The chart notes alcohol use, tobacco use, pesticide exposure, prior malignancy (patient or family), and no prior skin cancer (patient or family); a clinical close-up photograph of a skin lesion; the patient was assessed as Fitzpatrick II — 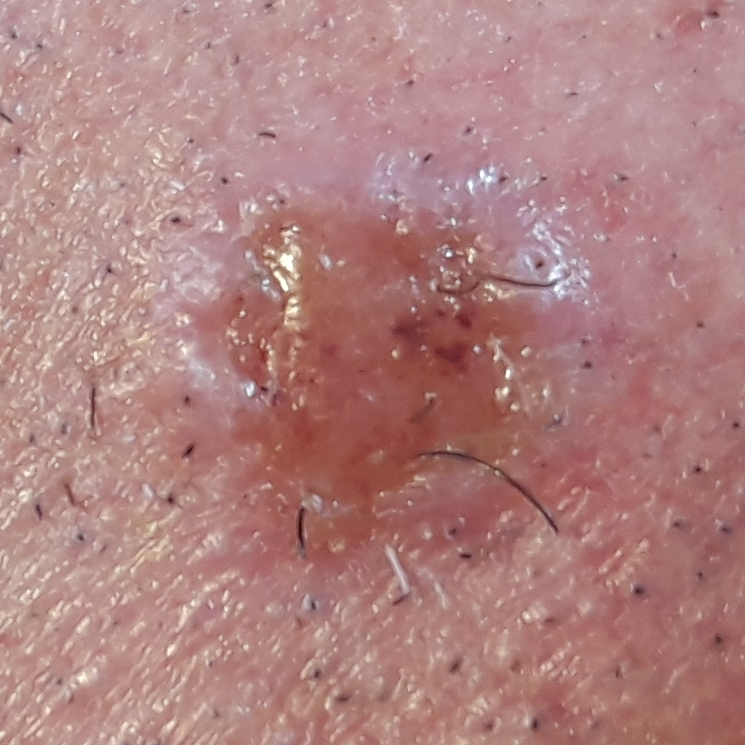body site — the face; size — 12x12 mm; patient-reported symptoms — elevation, growth, itching, bleeding, pain; diagnostic label — basal cell carcinoma (biopsy-proven).